A dermoscopy image of a single skin lesion:
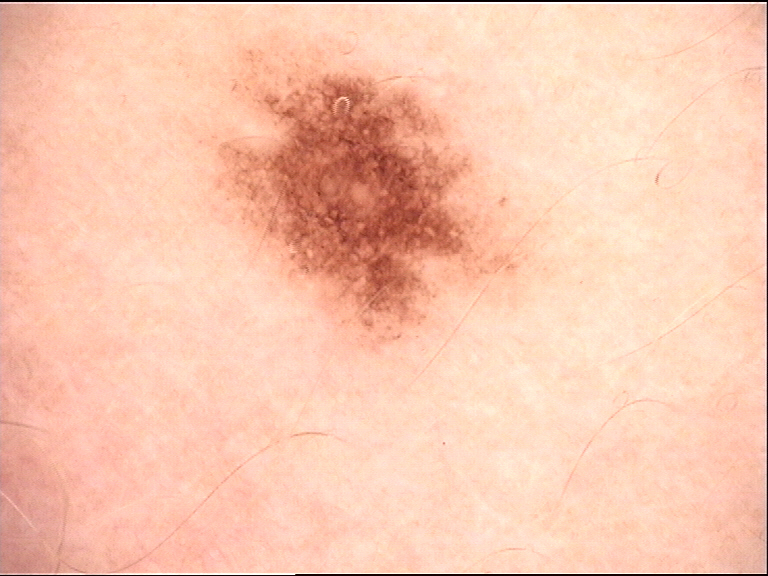The morphology is that of a banal lesion. Classified as a junctional nevus.